A dermoscopic view of a skin lesion:
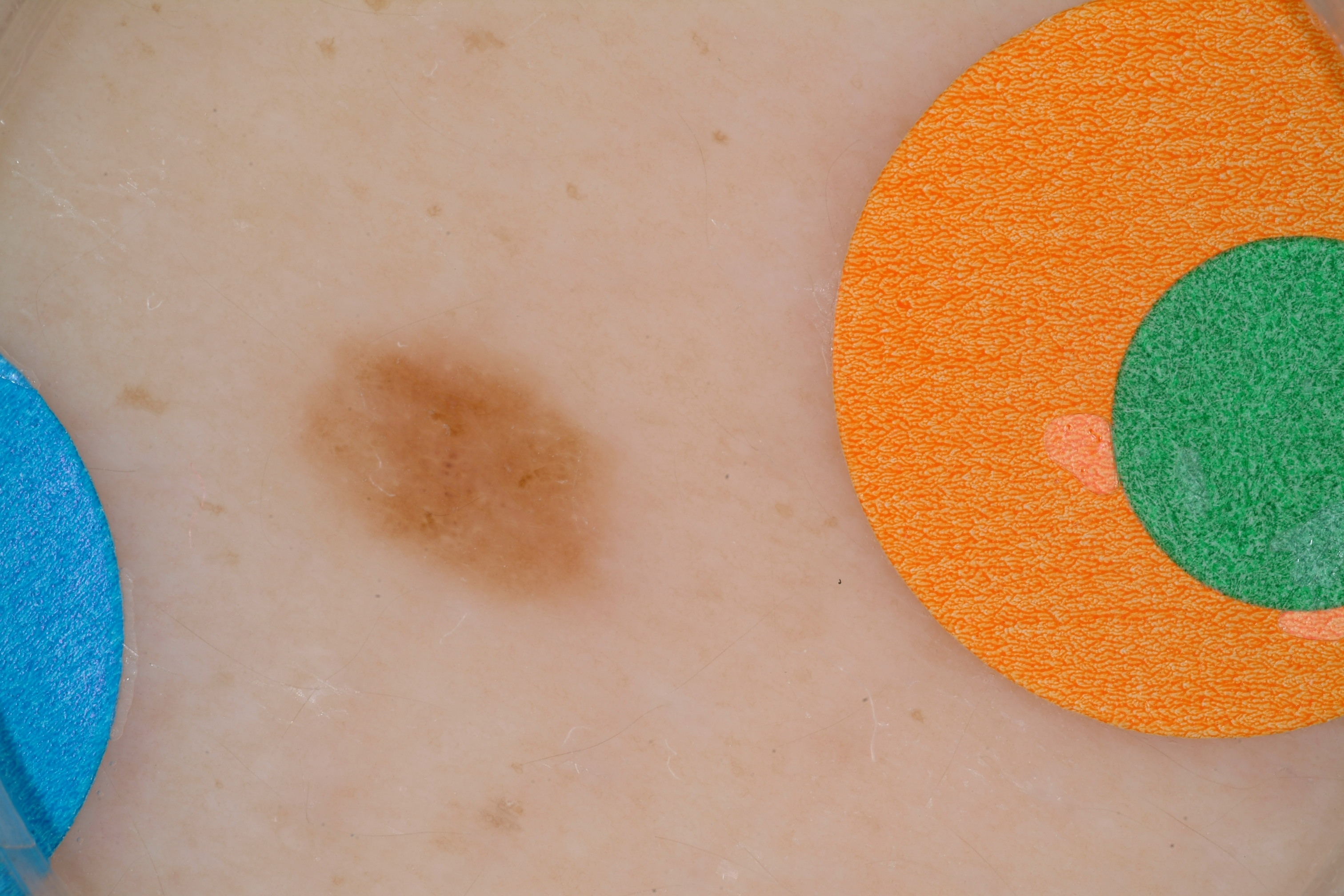Notes:
* dermoscopic pattern: globules
* lesion location: left=286, top=323, right=633, bottom=619
* impression: a benign lesion